A clinical close-up photograph of a skin lesion. A female subject 73 years old:
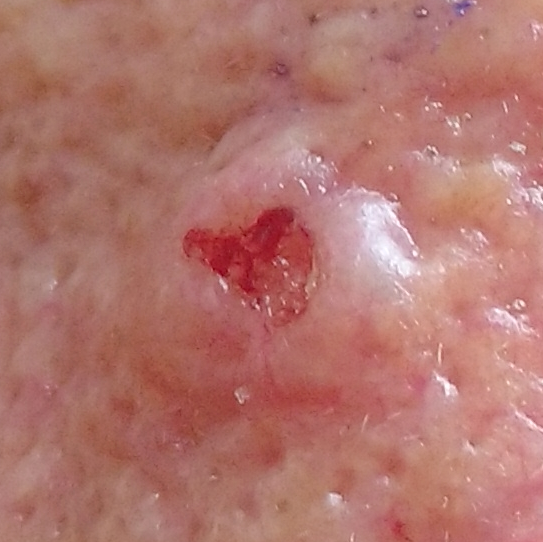Patient and lesion:
Located on the nose. Per patient report, the lesion hurts, itches, is elevated, and has bled.
Diagnosis:
Confirmed on histopathology as a basal cell carcinoma.